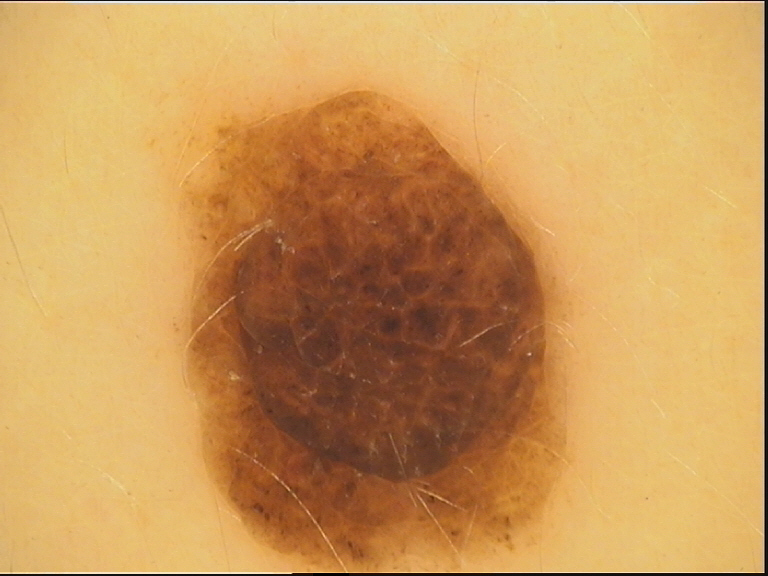A dermoscopy image of a single skin lesion. The diagnostic label was a compound nevus.